A dermatoscopic image of a skin lesion · the patient is a male approximately 20 years of age: 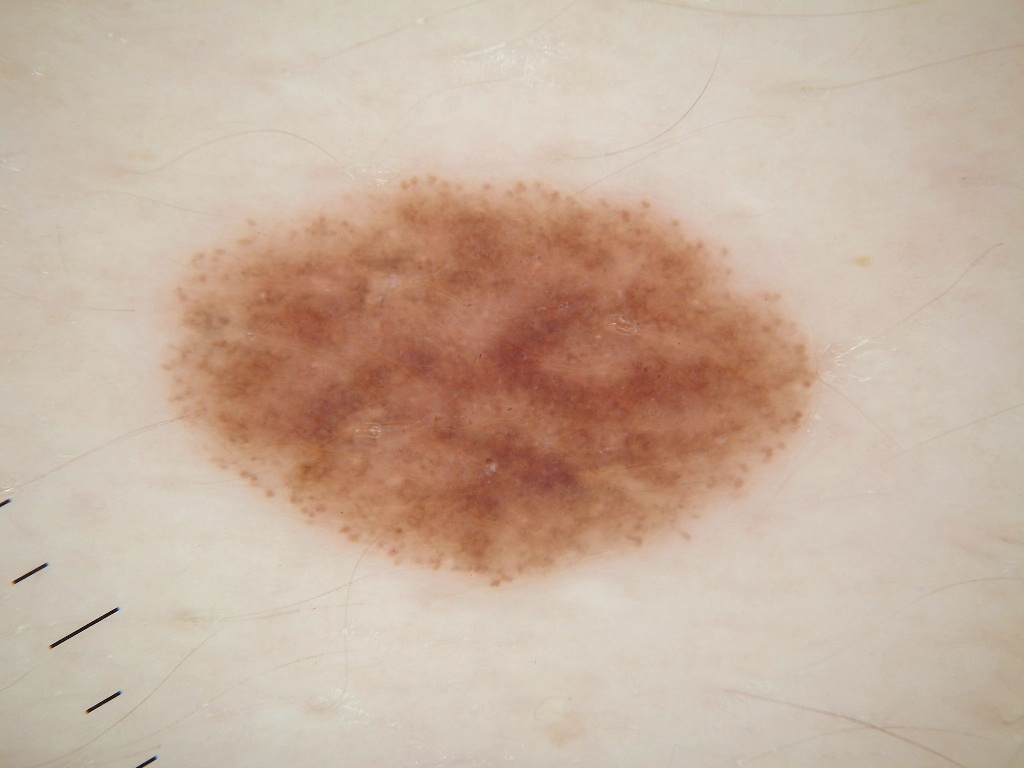The lesion covers approximately 27% of the dermoscopic field.
The dermoscopic pattern shows milia-like cysts and pigment network.
In (x1, y1, x2, y2) order, lesion location: 150, 171, 837, 590.
The clinical diagnosis was a melanocytic nevus.